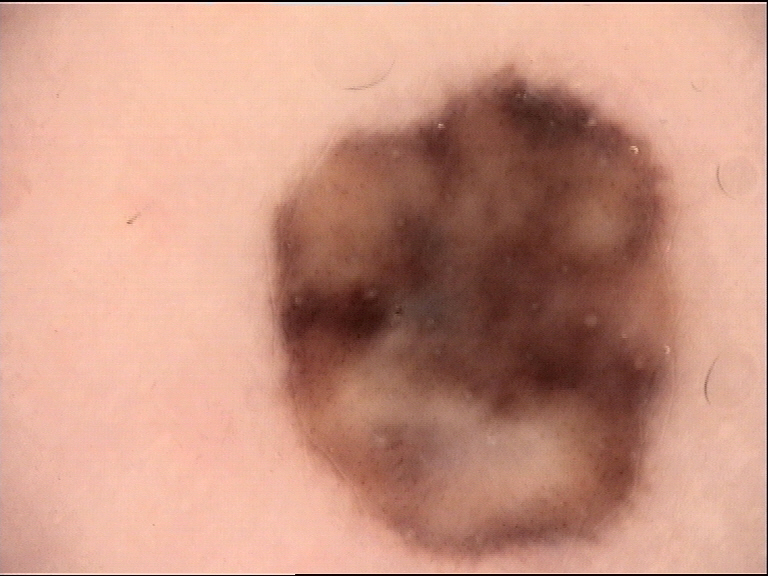| field | value |
|---|---|
| modality | dermoscopy |
| class | blue nevus (expert consensus) |